This is a close-up image. The contributor is a female aged 40–49. The affected area is the arm:
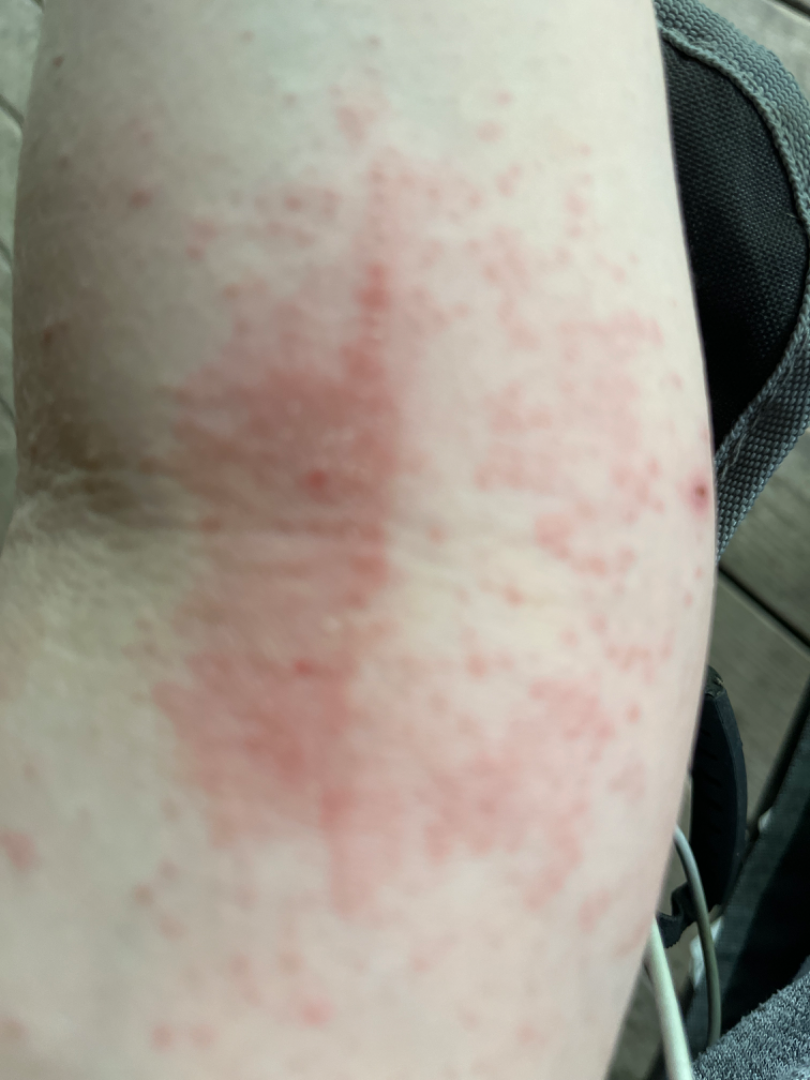History: Present for one to four weeks. The lesion is described as raised or bumpy. No constitutional symptoms were reported. Impression: On remote review of the image: the leading consideration is Eczema; possibly Allergic Contact Dermatitis; lower on the differential is Drug Rash.